This is a dermoscopic photograph of a skin lesion.
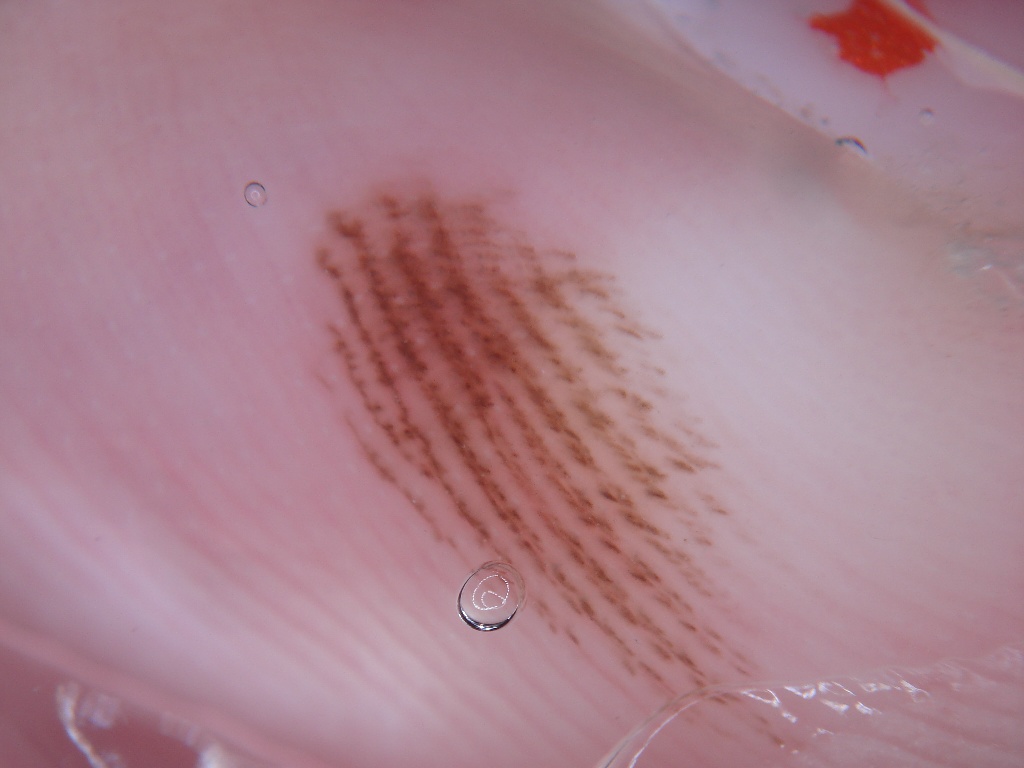Summary:
Lesion location: bbox=[278, 159, 803, 757].
Conclusion:
Diagnosed as a benign lesion.